The contributor reports the lesion is rough or flaky and raised or bumpy · symptoms reported: itching and burning · the patient is a female aged 40–49 · the lesion involves the head or neck, arm, front of the torso and palm · associated systemic symptoms include shortness of breath and mouth sores · reported duration is one to three months · an image taken at an angle · self-categorized by the patient as a rash.
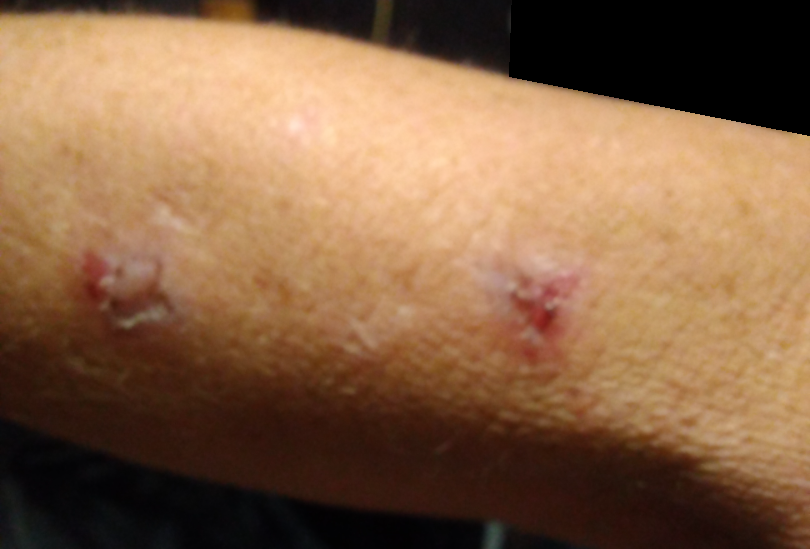| feature | finding |
|---|---|
| assessment | ungradable on photographic review |